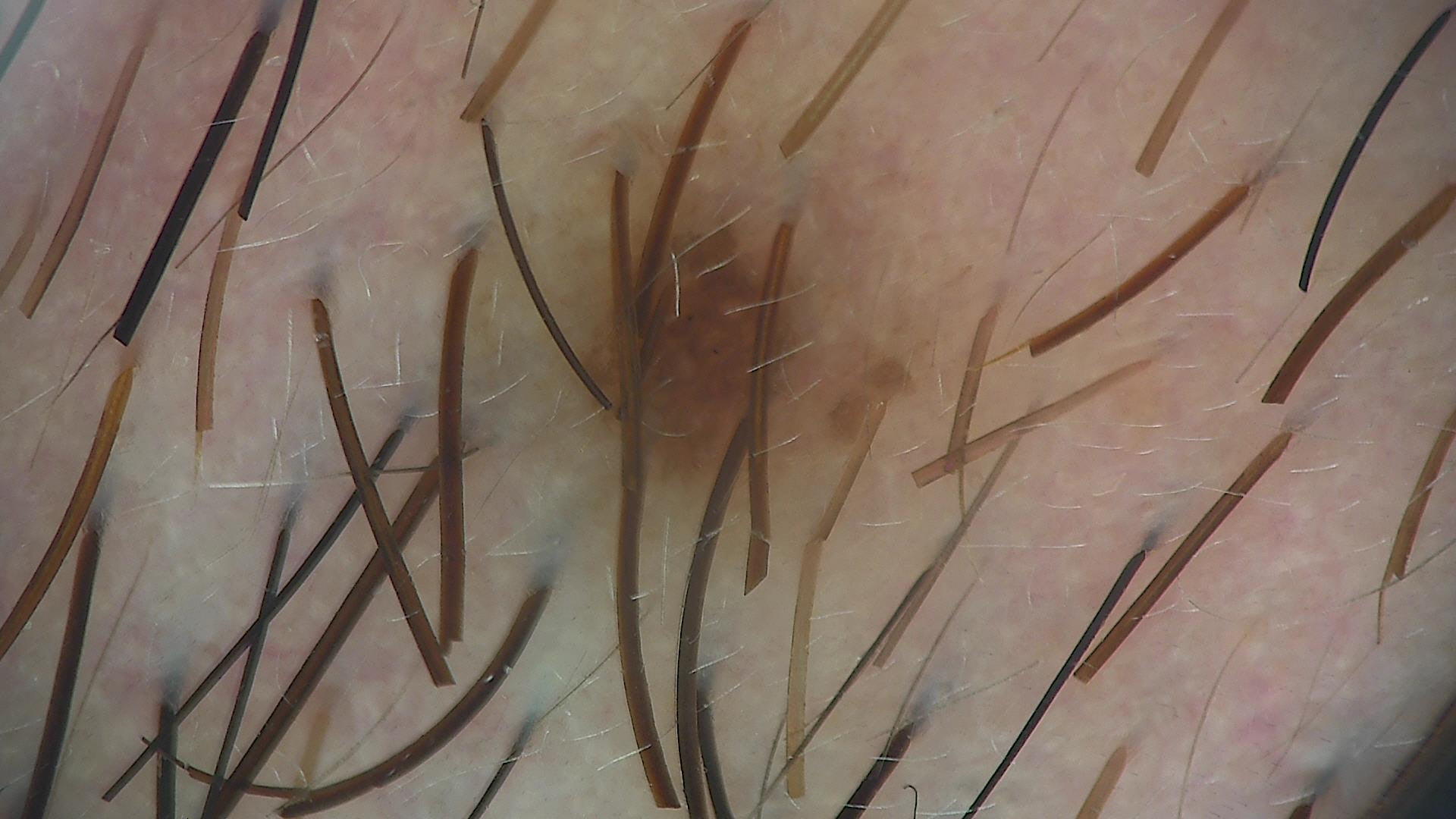Q: What is the diagnosis?
A: compound nevus (expert consensus)